A dermoscopic image of a skin lesion · a female patient aged 78-82 · recorded as Fitzpatrick II: 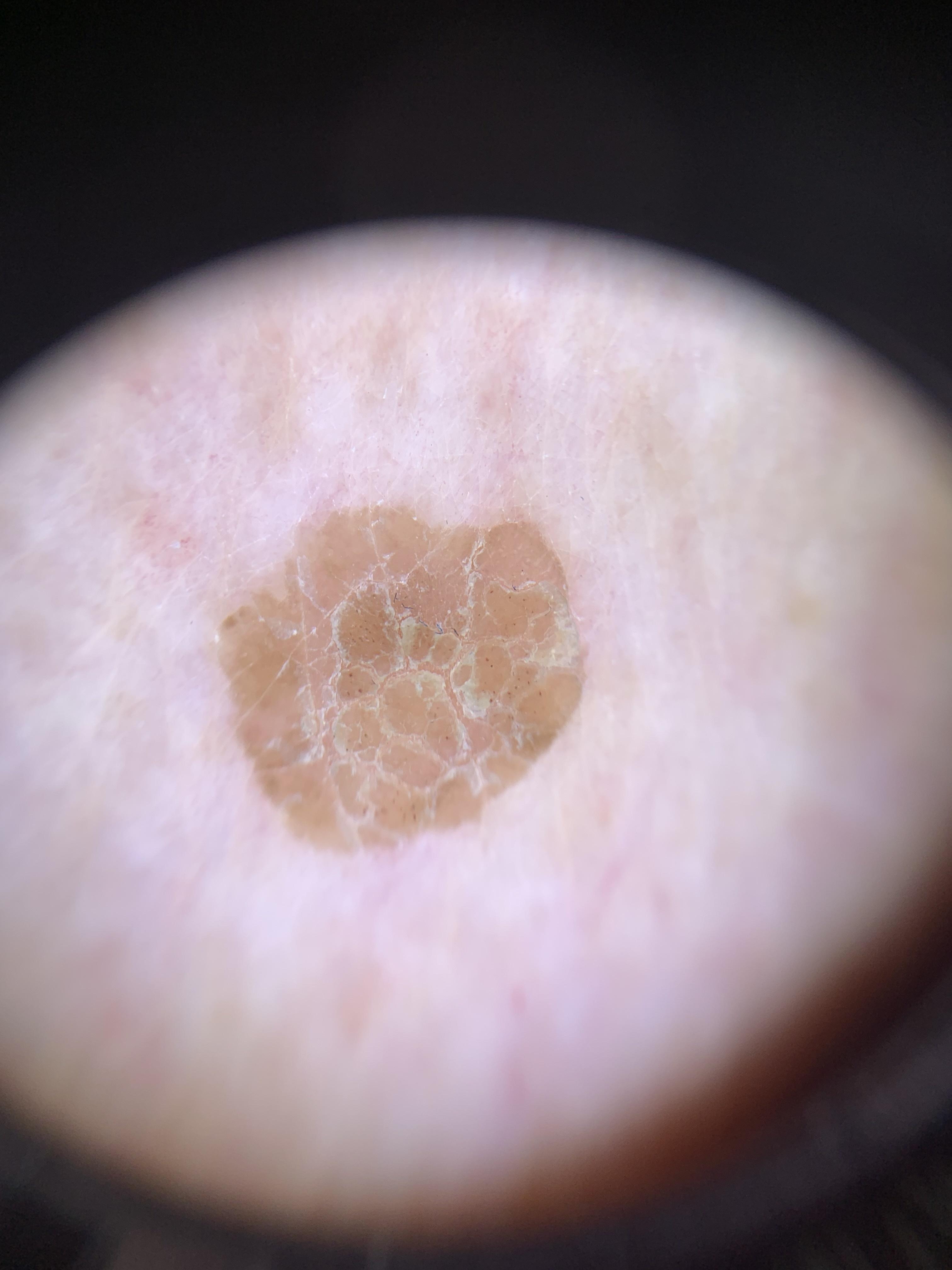anatomic site: a lower extremity; assessment: Seborrheic keratosis.